A female subject in their 60s; Fitzpatrick skin type II — 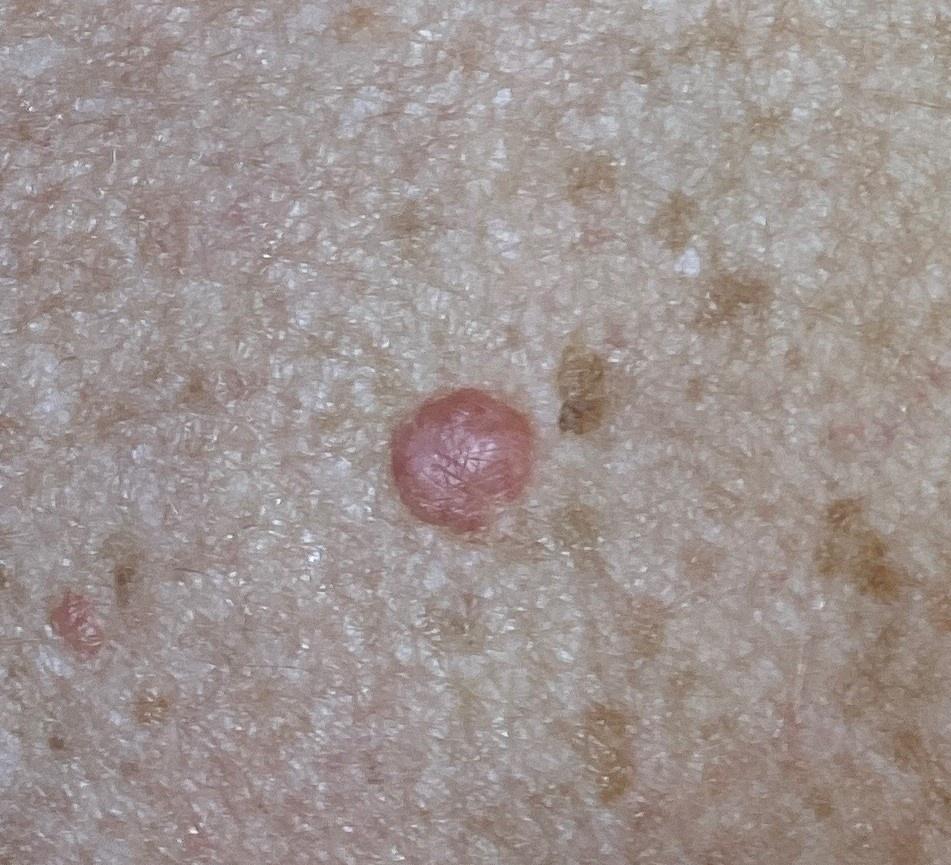site: the trunk | pathology: Nevus (biopsy-proven).